This is a close-up image · texture is reported as raised or bumpy and flat · the patient described the issue as a rash · reported lesion symptoms include bothersome appearance · the affected area is the head or neck · no associated systemic symptoms reported:
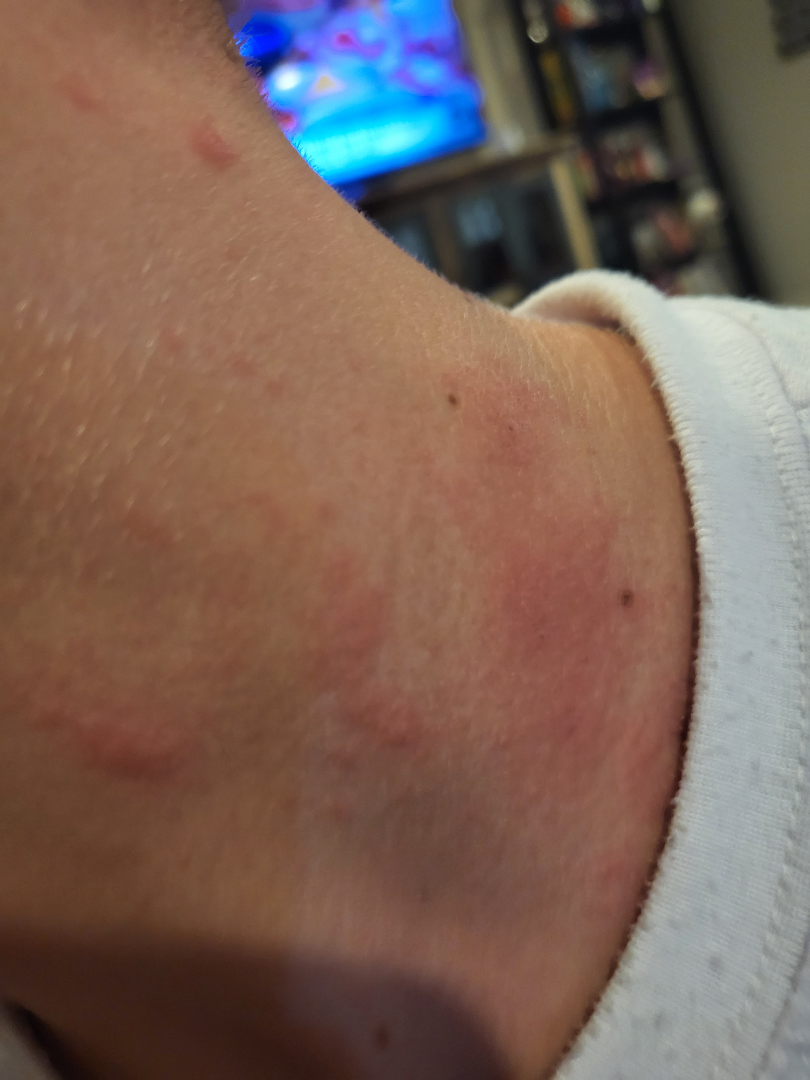Findings:
The leading impression is Allergic Contact Dermatitis; an alternative is Urticaria.